By self-report, immunosuppression and a prior organ transplant; the patient says their skin reddens painfully with sun exposure; a female patient aged 55; acquired for a research image collection, with no referral diagnosis; a dermoscopic image of a skin lesion: 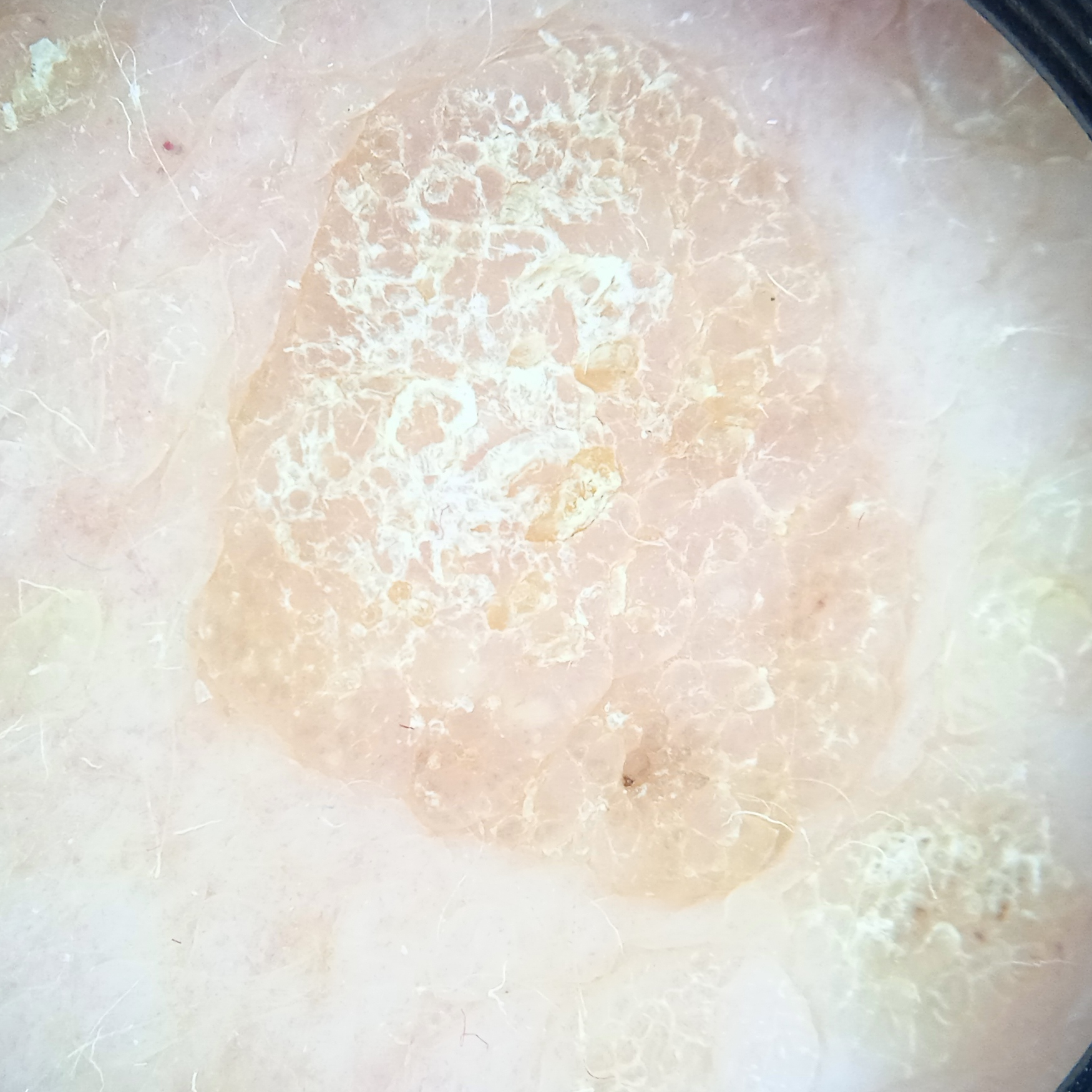anatomic site: the back; lesion size: 10.6 mm; assessment: seborrheic keratosis (dermatologist consensus).